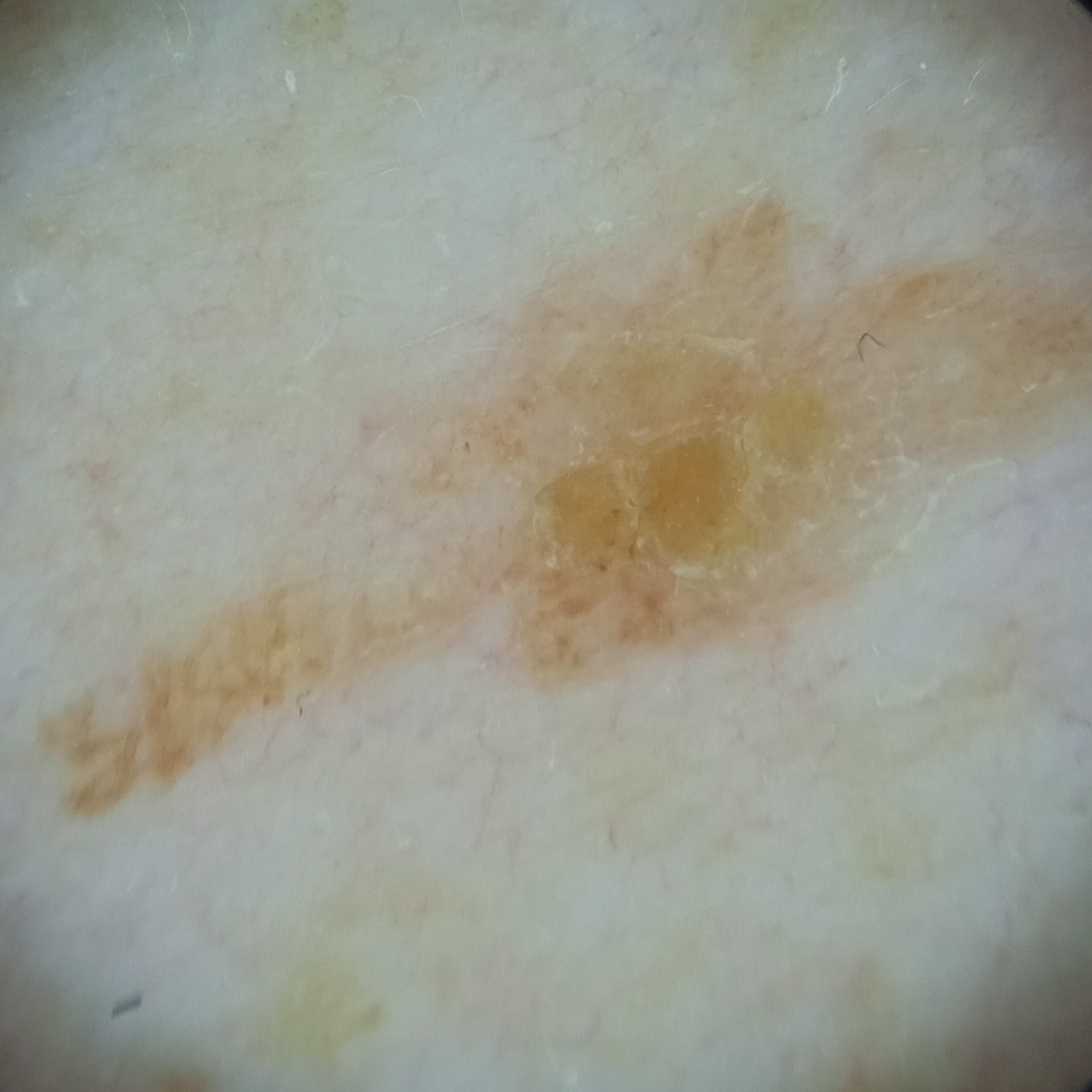A male subject 83 years old. Acquired for a research image collection, with no referral diagnosis. A dermatoscopic image of a skin lesion. The patient says their skin reddens with sun exposure. Located on the back. Measuring roughly 16.4 mm. The diagnostic impression was a seborrheic keratosis.